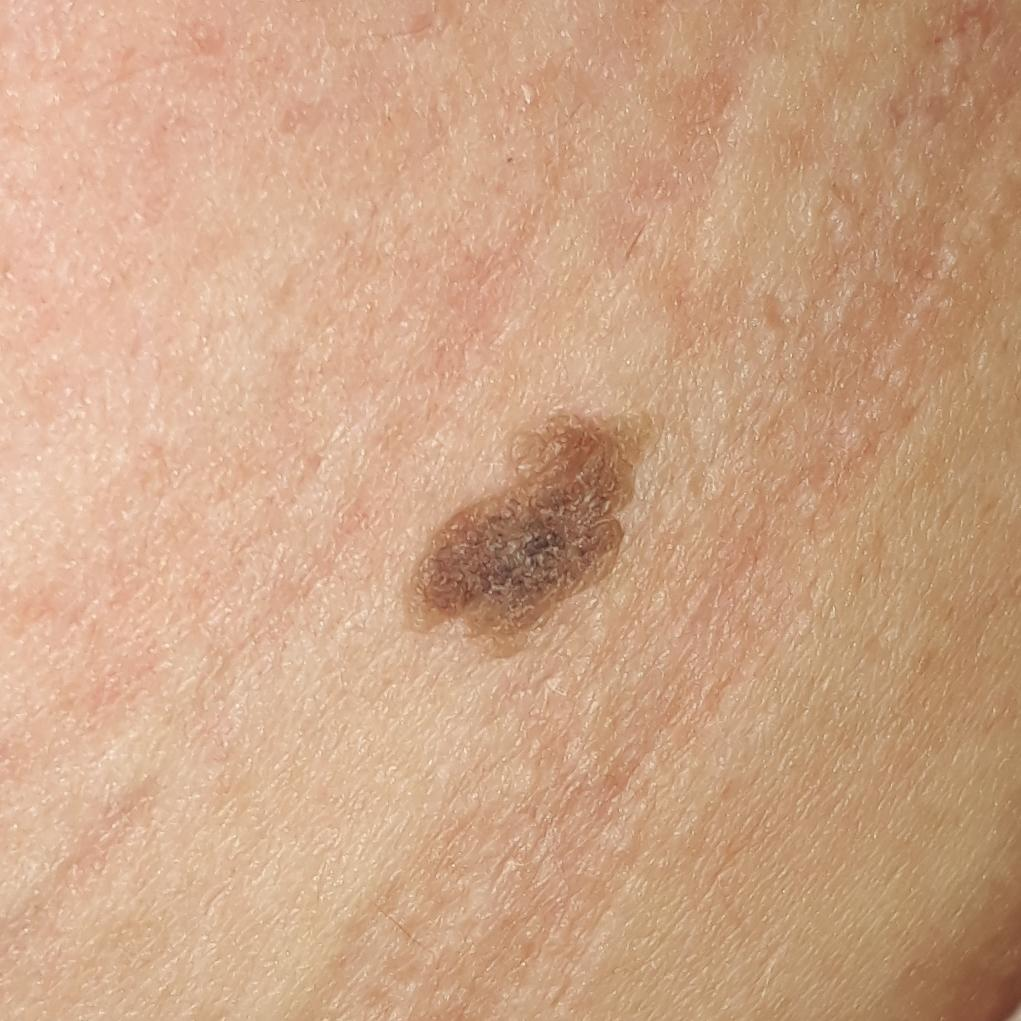Patient and lesion:
A clinical close-up photograph of a skin lesion. The lesion is located on the abdomen. Per patient report, the lesion has grown and is elevated.
Conclusion:
The diagnostic impression was a seborrheic keratosis.